A dermatoscopic image of a skin lesion. A female patient in their 50s.
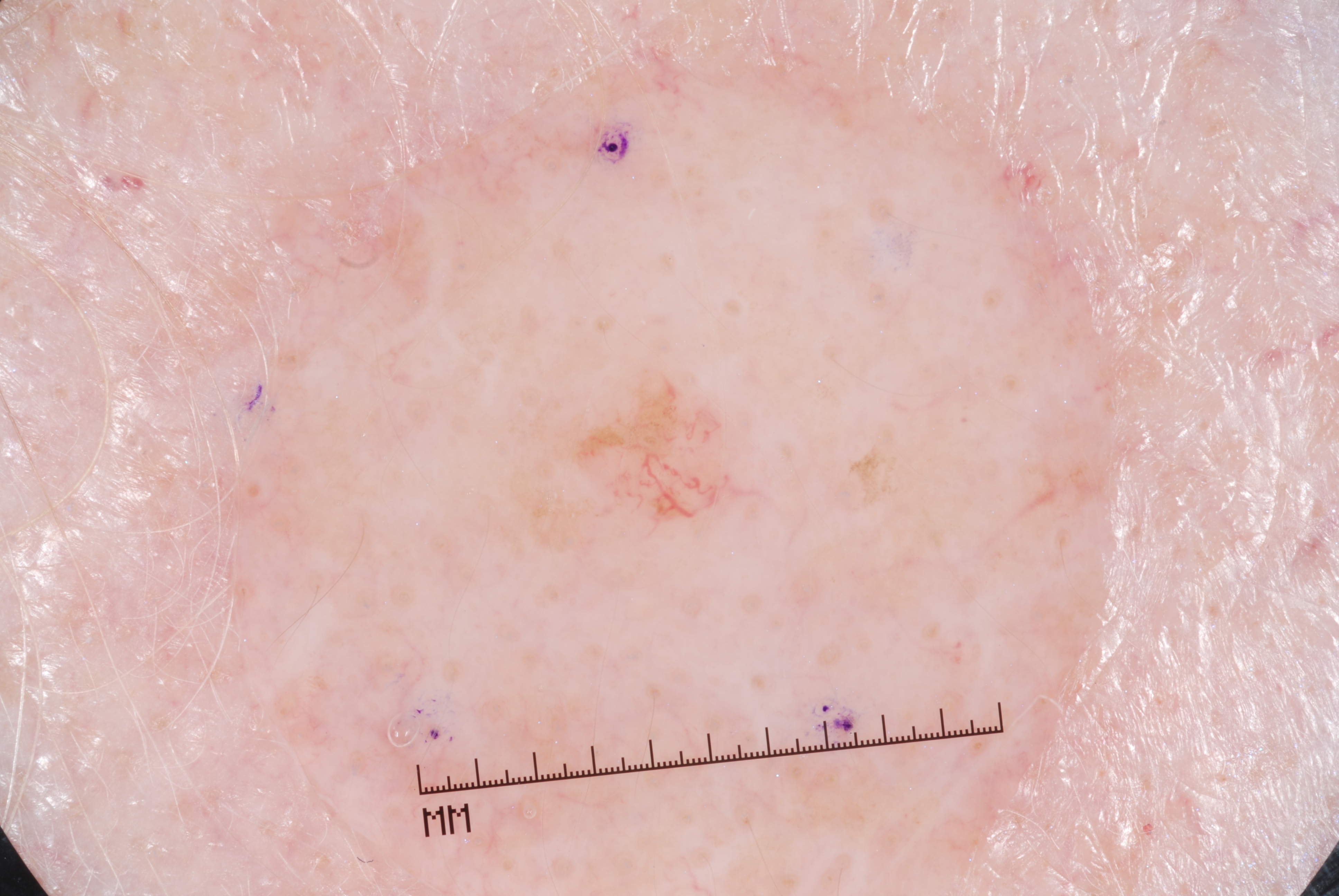Case summary: Dermoscopic examination shows no milia-like cysts, streaks, pigment network, or negative network. As (left, top, right, bottom), the lesion occupies the region [492, 349, 765, 561]. Impression: The diagnostic assessment was a melanocytic nevus.